A subject 63 years of age. A clinical photograph of a skin lesion:
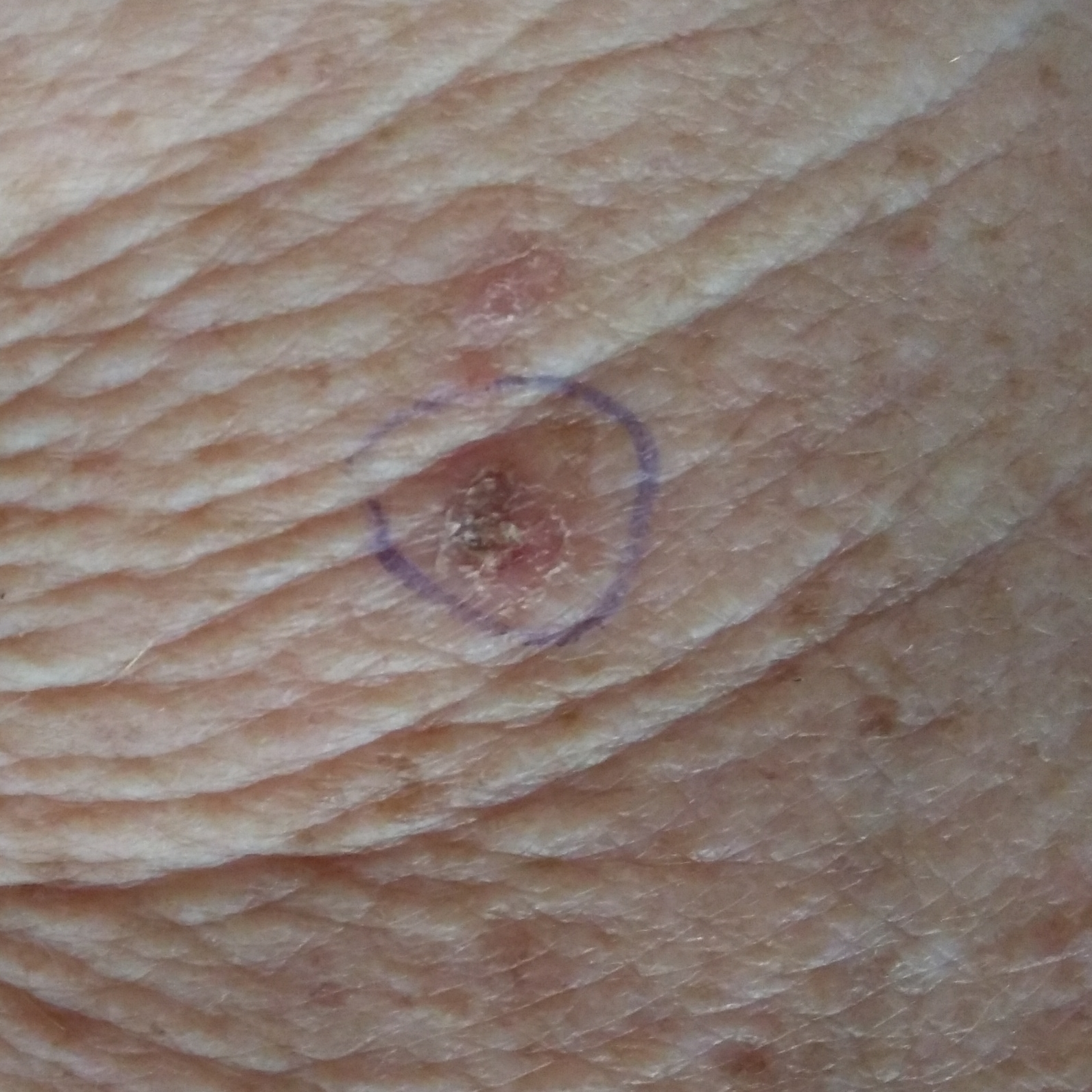anatomic site = a hand | reported symptoms = itching, elevation | diagnostic label = actinic keratosis (clinical consensus).